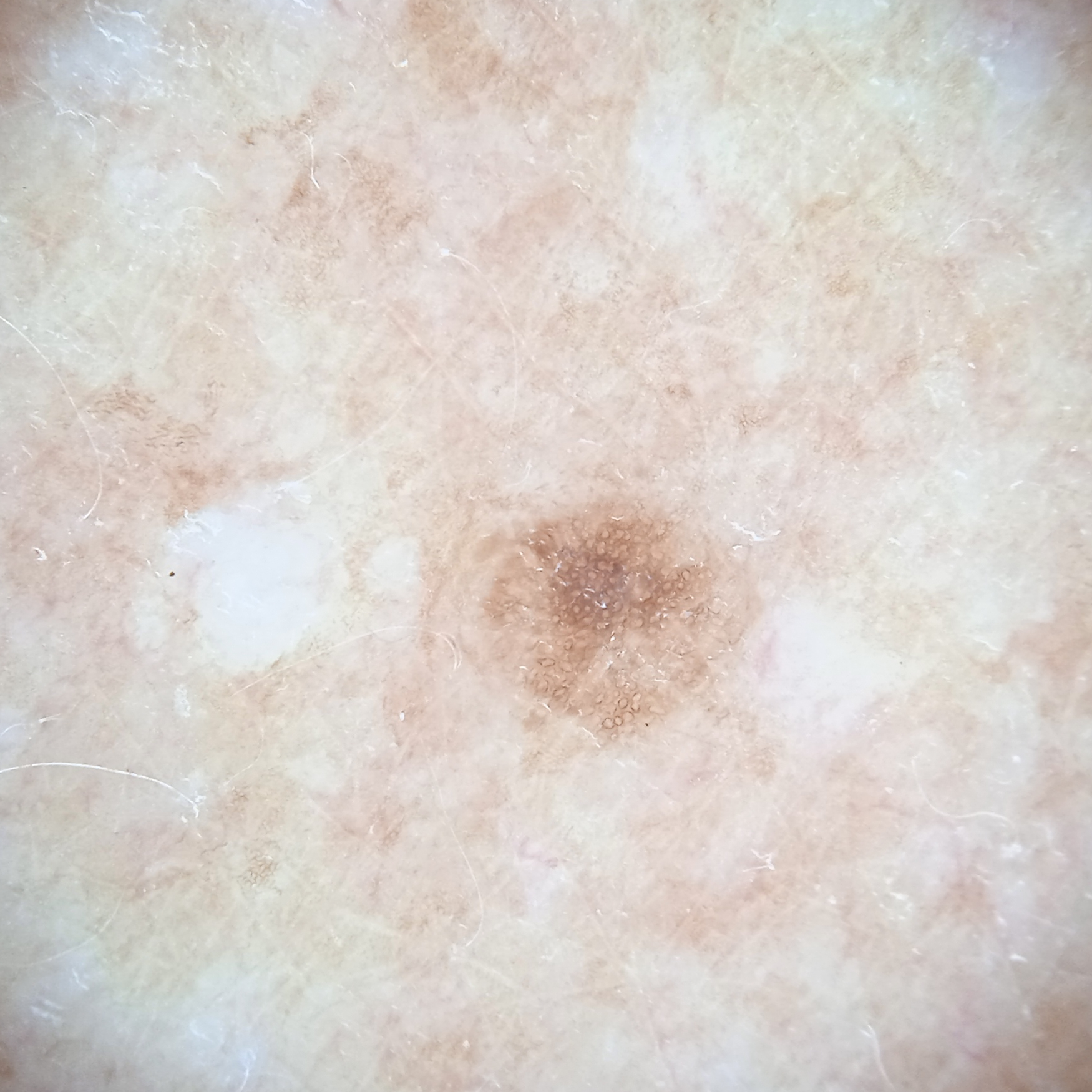<skin_lesion>
  <risk_factors>
    <positive>a personal history of cancer, a personal history of skin cancer</positive>
  </risk_factors>
  <mole_burden>a moderate number of melanocytic nevi</mole_burden>
  <patient>
    <age>75</age>
    <sex>female</sex>
  </patient>
  <lesion_size>
    <diameter_mm>2.7</diameter_mm>
  </lesion_size>
  <diagnosis>
    <name>melanocytic nevus</name>
    <malignancy>benign</malignancy>
  </diagnosis>
</skin_lesion>